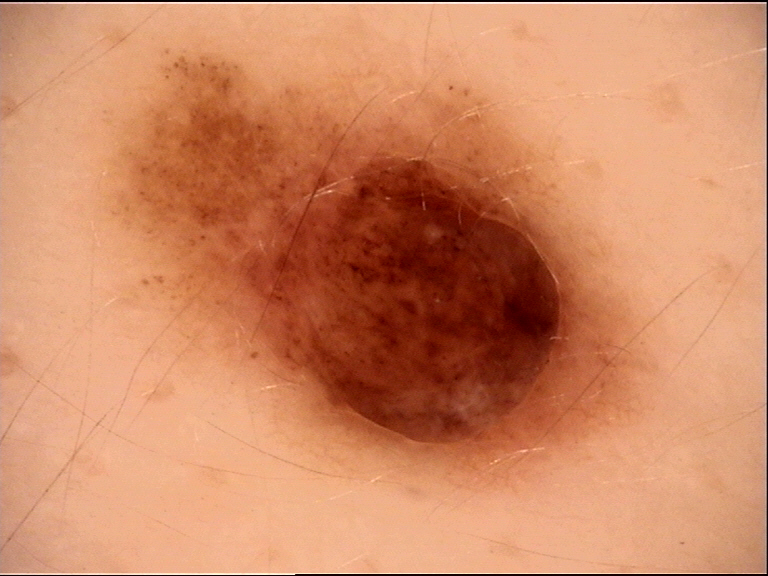{"image": "dermoscopy", "lesion_type": {"main_class": "banal", "pattern": "compound"}, "diagnosis": {"name": "compound nevus", "code": "cb", "malignancy": "benign", "super_class": "melanocytic", "confirmation": "expert consensus"}}